History notes prior skin cancer (patient or family), pesticide exposure, prior malignancy (patient or family), and no alcohol use · a male subject age 73 · a clinical photo of a skin lesion taken with a smartphone · the patient was assessed as skin type II:
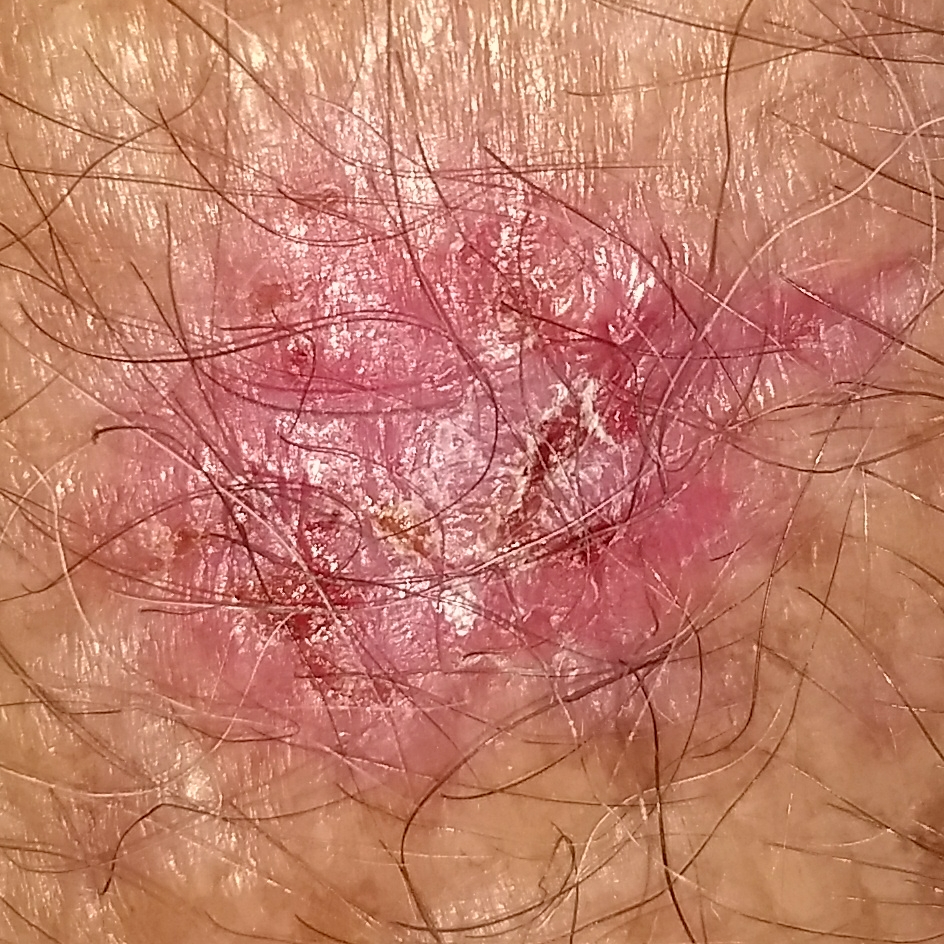Clinical context: The lesion is on a forearm. The lesion measures 15 × 10 mm. Per patient report, the lesion hurts, is elevated, has bled, and itches, but has not grown. Conclusion: Histopathologically confirmed as a basal cell carcinoma.